The patient considered this a rash. No relevant systemic symptoms. The subject is female. Reported lesion symptoms include itching and bothersome appearance. Reported duration is one to three months. The lesion is described as raised or bumpy and rough or flaky. The arm is involved. An image taken at a distance — 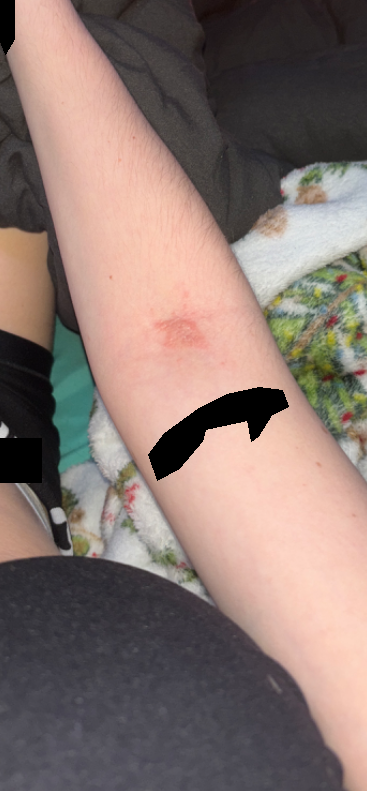On photographic review by a dermatologist: Eczema and Allergic Contact Dermatitis were each considered, in no particular order.